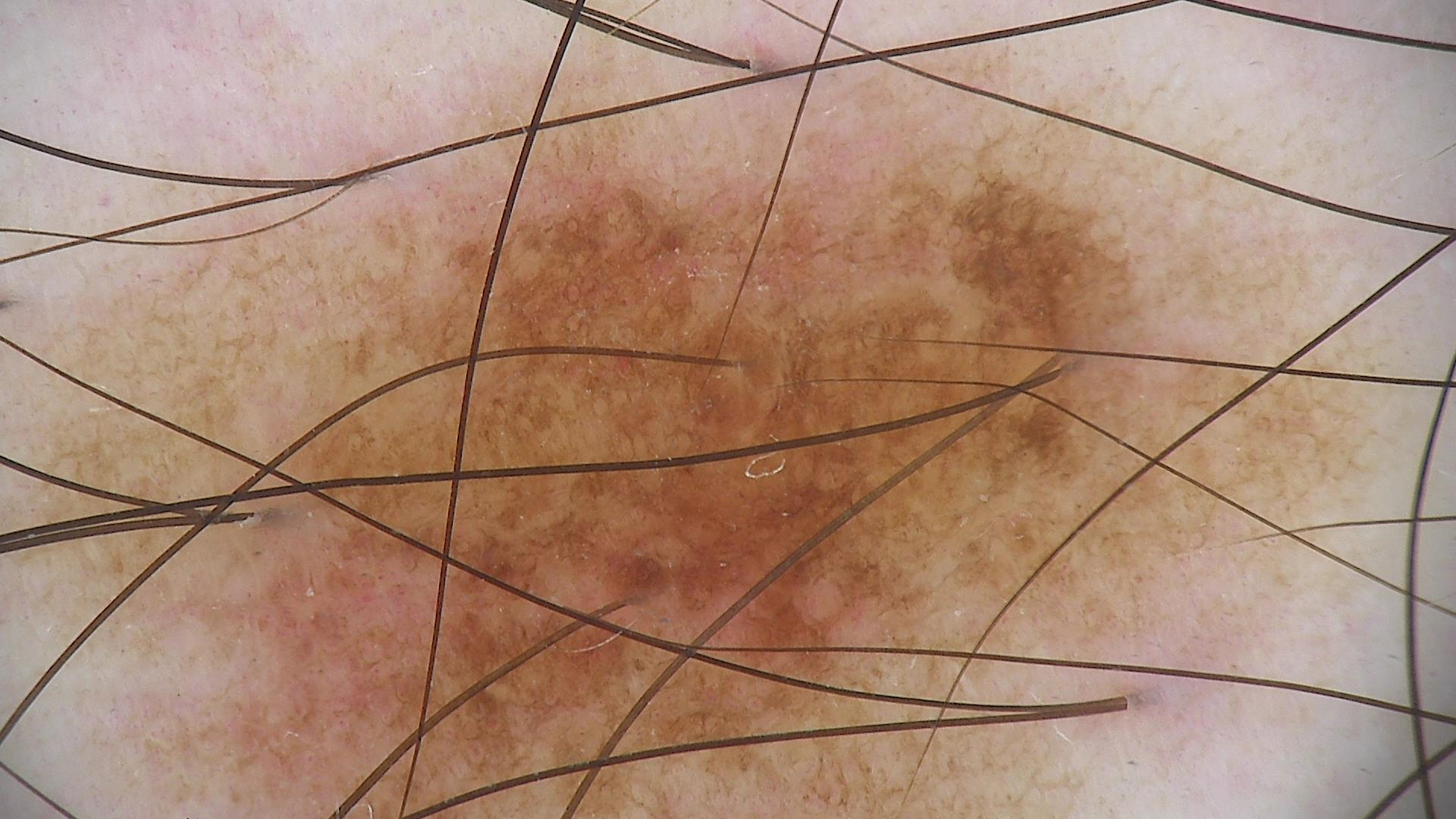Case: A dermoscopic photograph of a skin lesion. Impression: The diagnosis was a dysplastic junctional nevus.